A dermoscopy image of a single skin lesion.
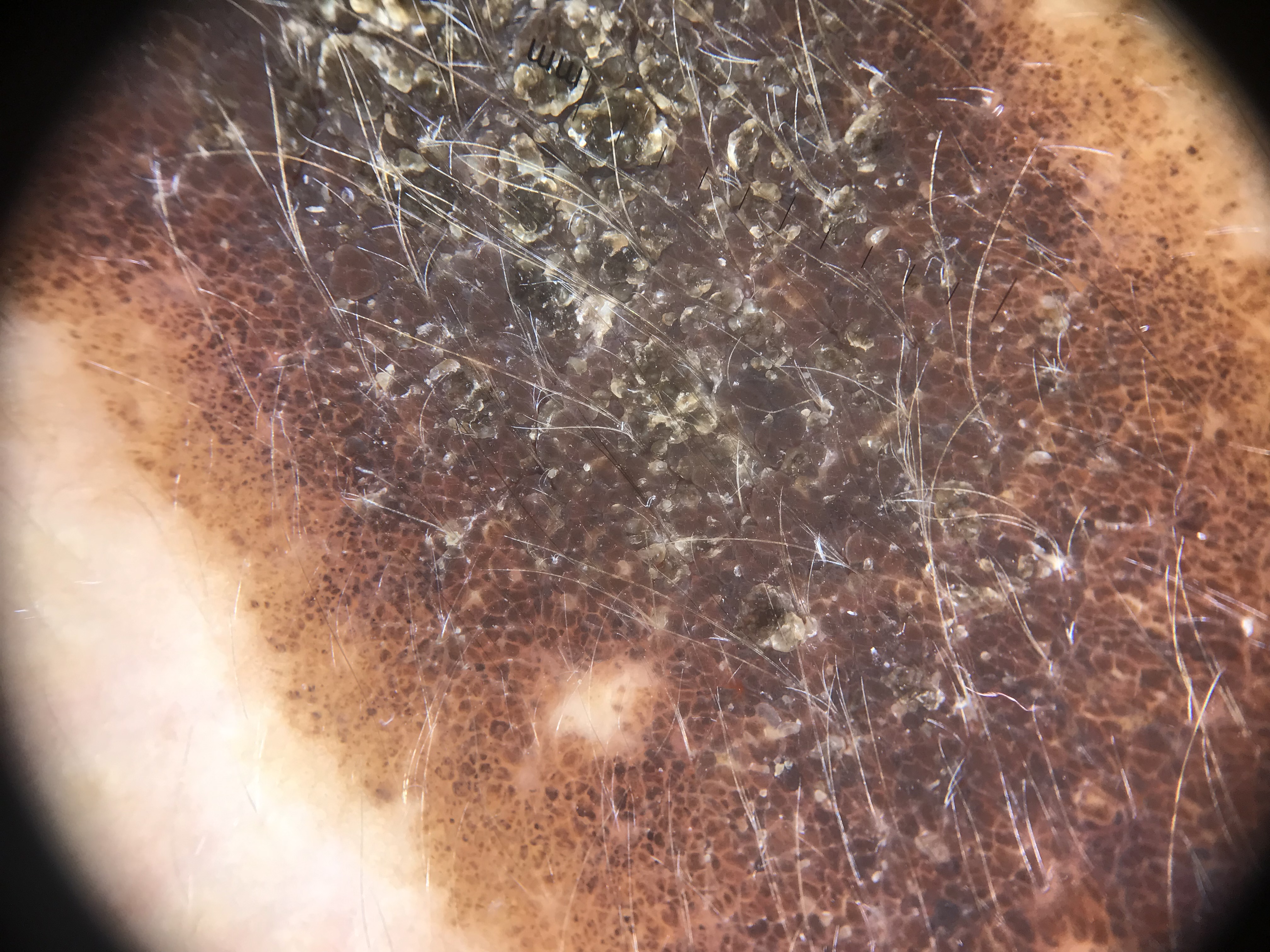This is a banal lesion.
The diagnosis was a congenital compound nevus.